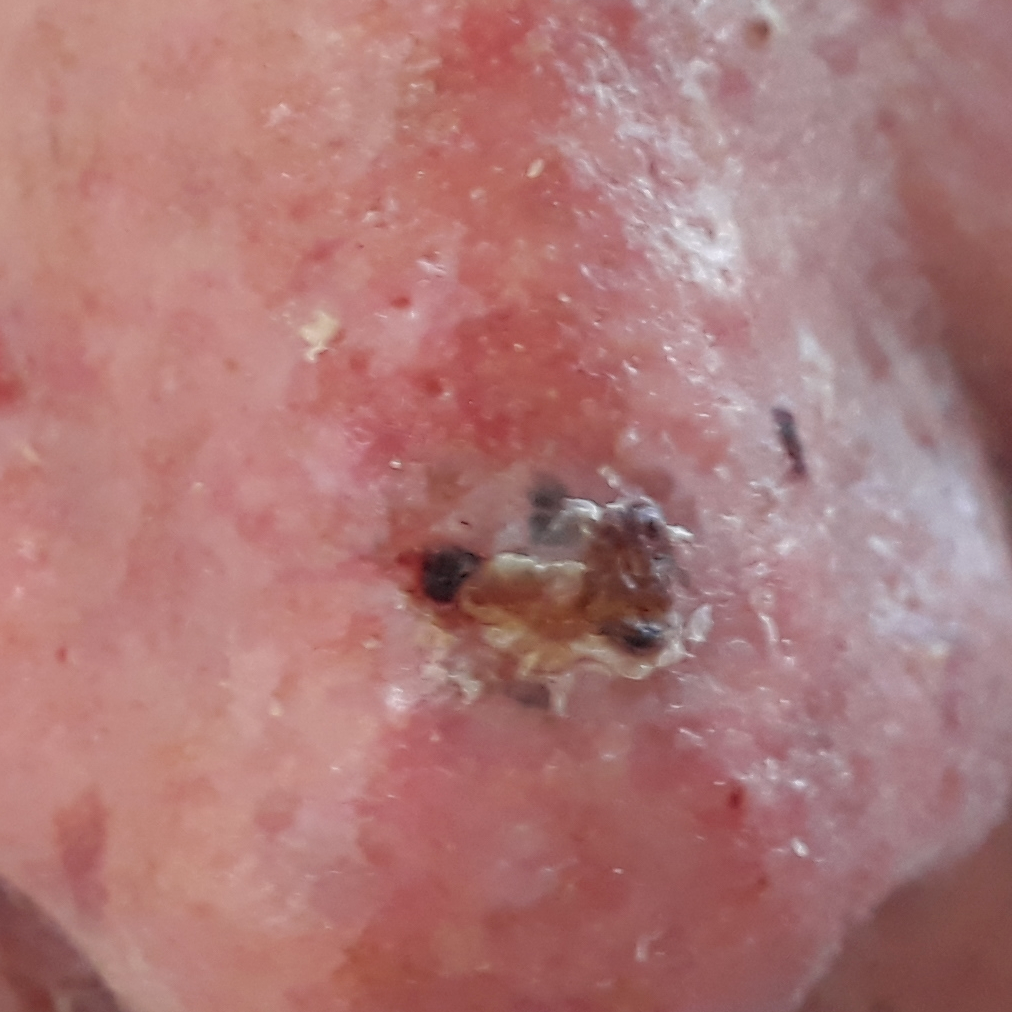| feature | finding |
|---|---|
| subject | male, aged 72 |
| location | the nose |
| diagnostic label | basal cell carcinoma (biopsy-proven) |